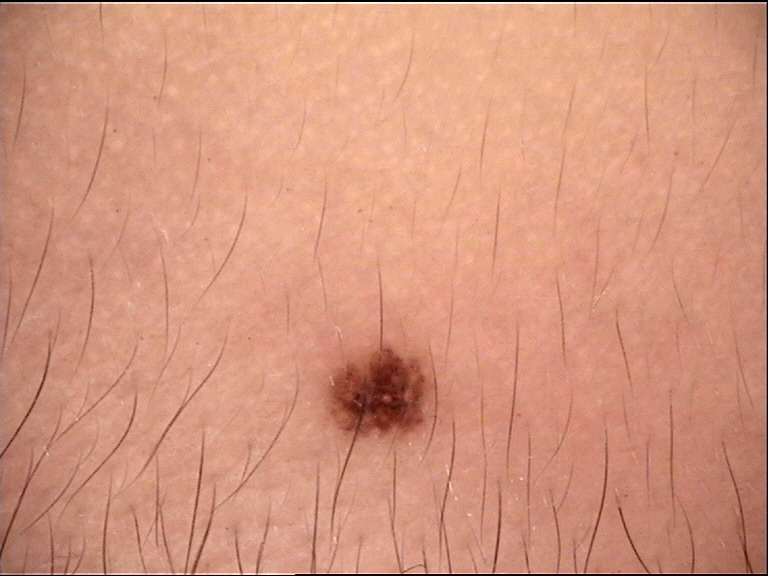Q: What is the imaging modality?
A: dermoscopy
Q: What was the diagnostic impression?
A: Miescher nevus (expert consensus)